A dermatoscopic image of a skin lesion · the chart notes a first-degree relative with melanoma but no previous melanoma · the patient is FST III · a female patient aged around 35: 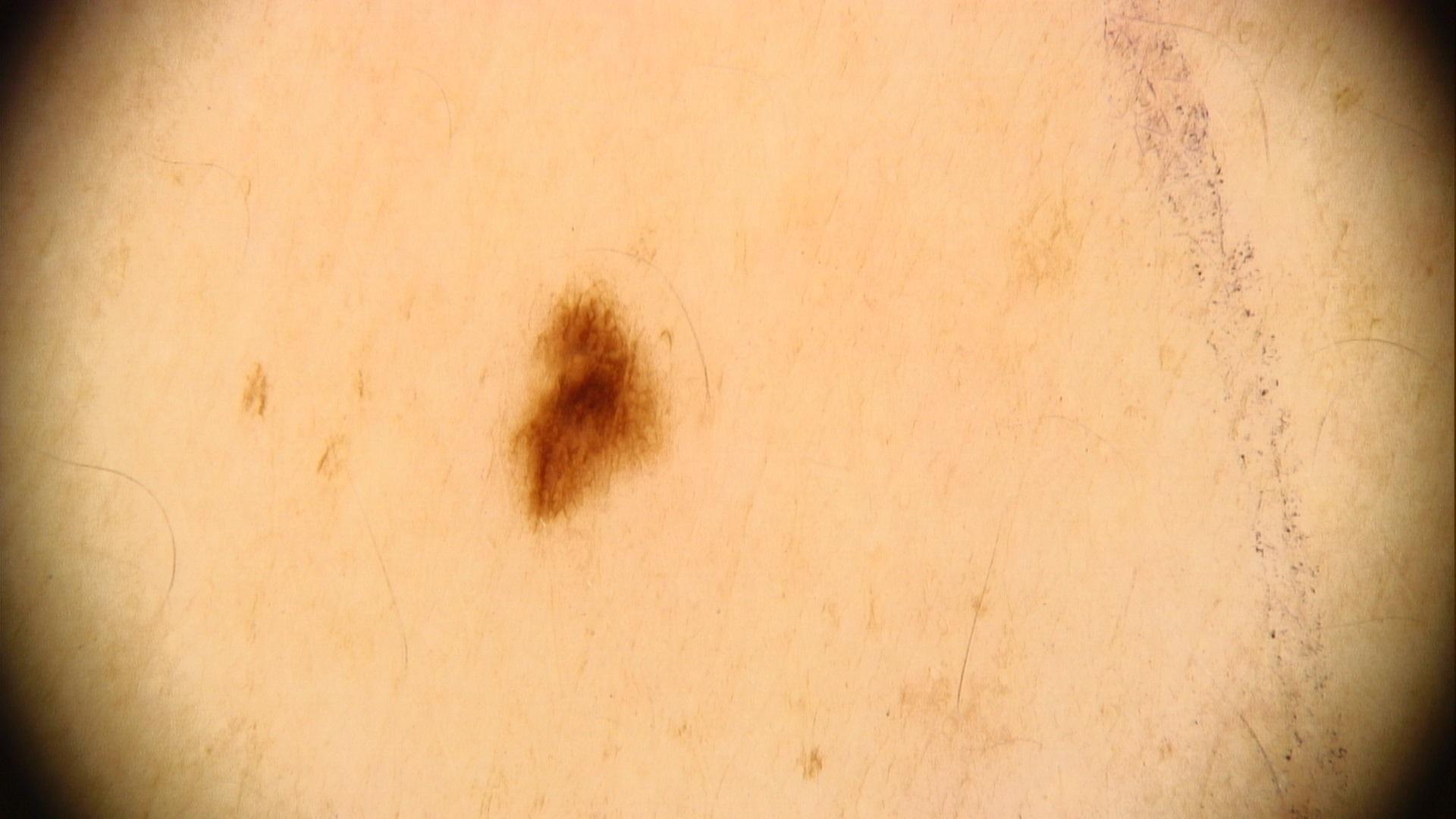Q: What is the anatomic site?
A: the trunk
Q: What is this lesion?
A: Nevus (clinical impression)